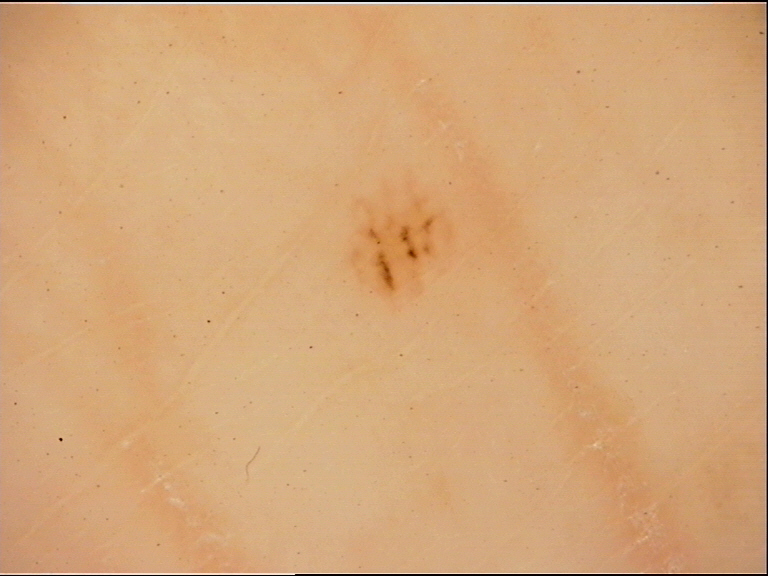Q: What kind of lesion is this?
A: banal
Q: What is this lesion?
A: acral junctional nevus (expert consensus)